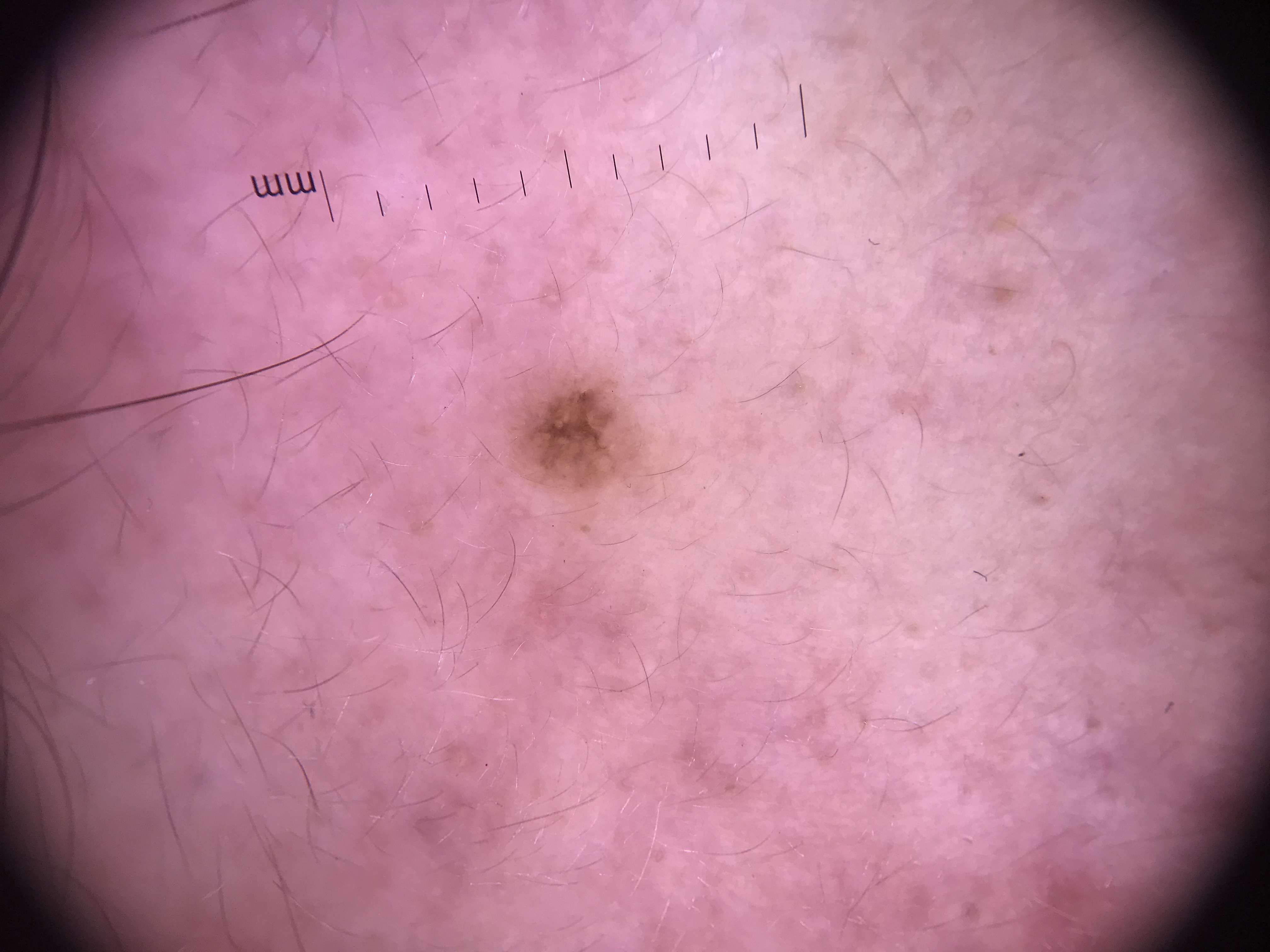A dermoscopic close-up of a skin lesion.
Labeled as a junctional nevus.